Symptoms reported: darkening, enlargement, burning, pain, bleeding, bothersome appearance and itching. The contributor notes the condition has been present for one to four weeks. The patient considered this a rash. The subject is female. The photograph was taken at an angle. The arm is involved. The contributor notes the lesion is raised or bumpy and rough or flaky: 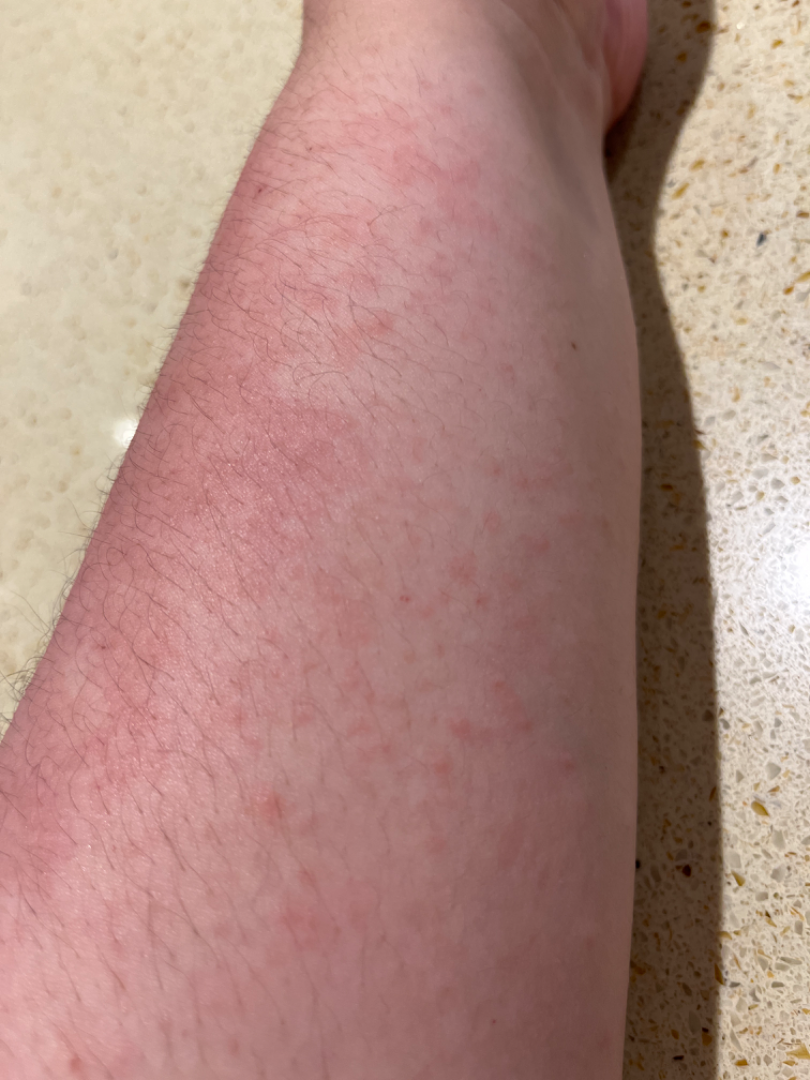Reviewed remotely by three dermatologists: most consistent with Eczema; also on the differential is Allergic Contact Dermatitis; a more distant consideration is Acute dermatitis, NOS; less likely is Hypersensitivity; less probable is Viral Exanthem; a remote consideration is Contact dermatitis, NOS.